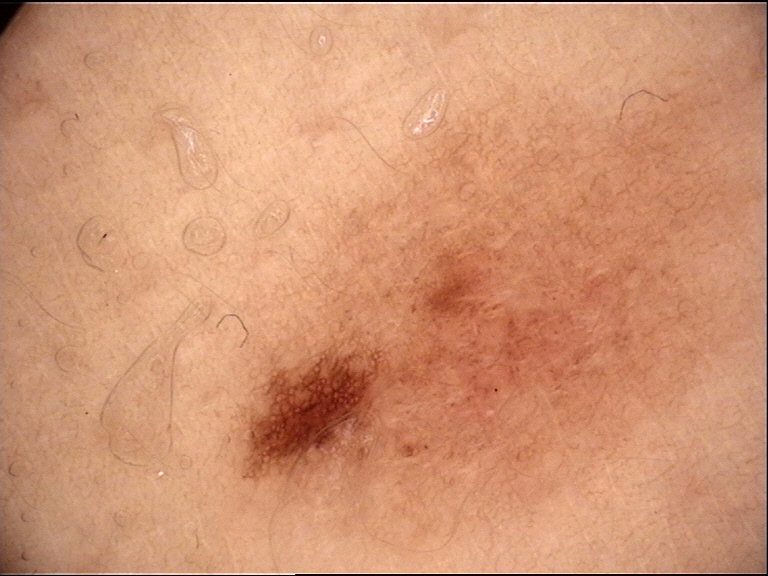class=dysplastic junctional nevus (expert consensus).